A dermoscopy image of a single skin lesion: 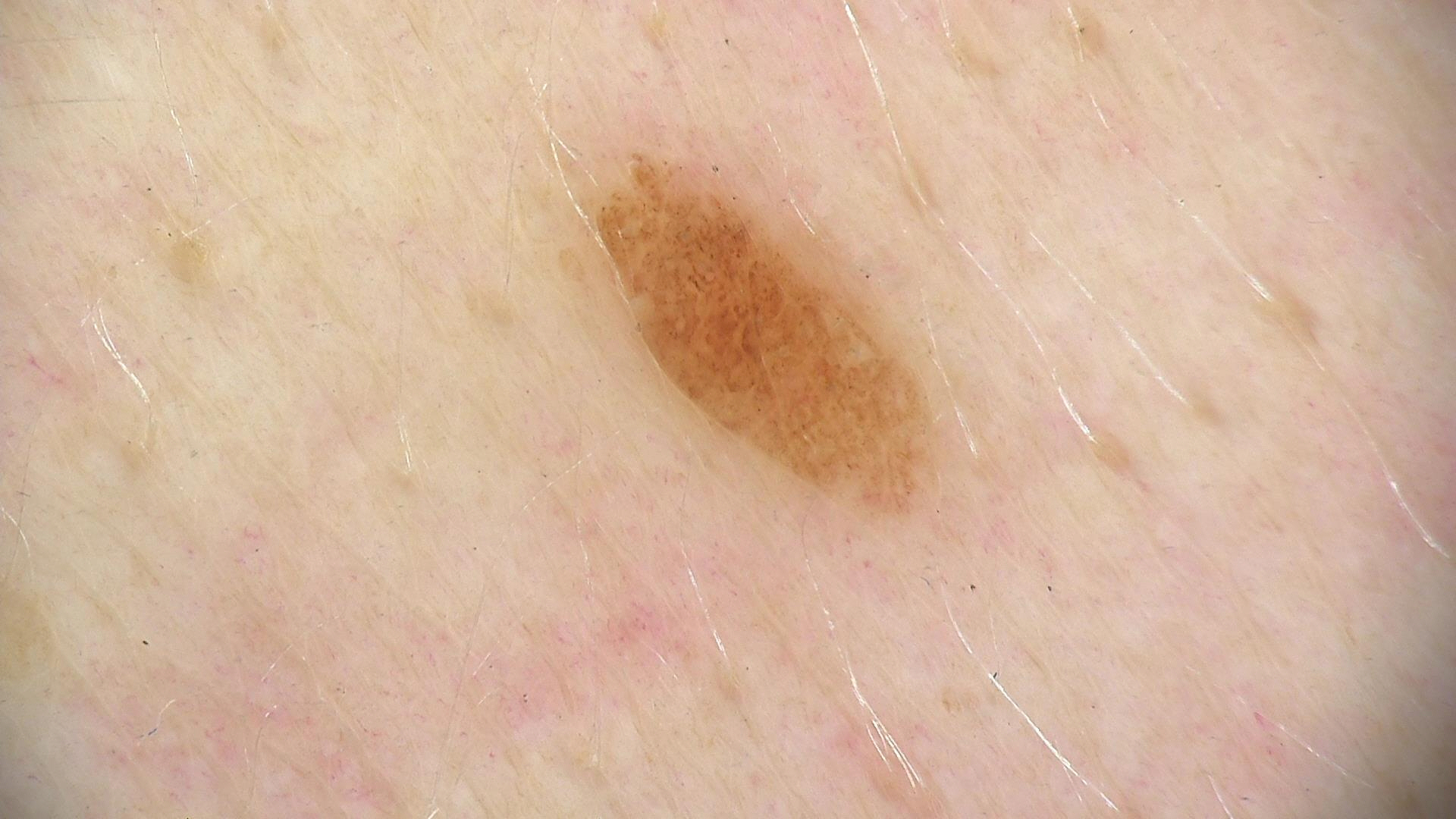This is a banal lesion.
The diagnostic label was a compound nevus.